The leg, back of the hand, arm and front of the torso are involved; the photo was captured at an angle — 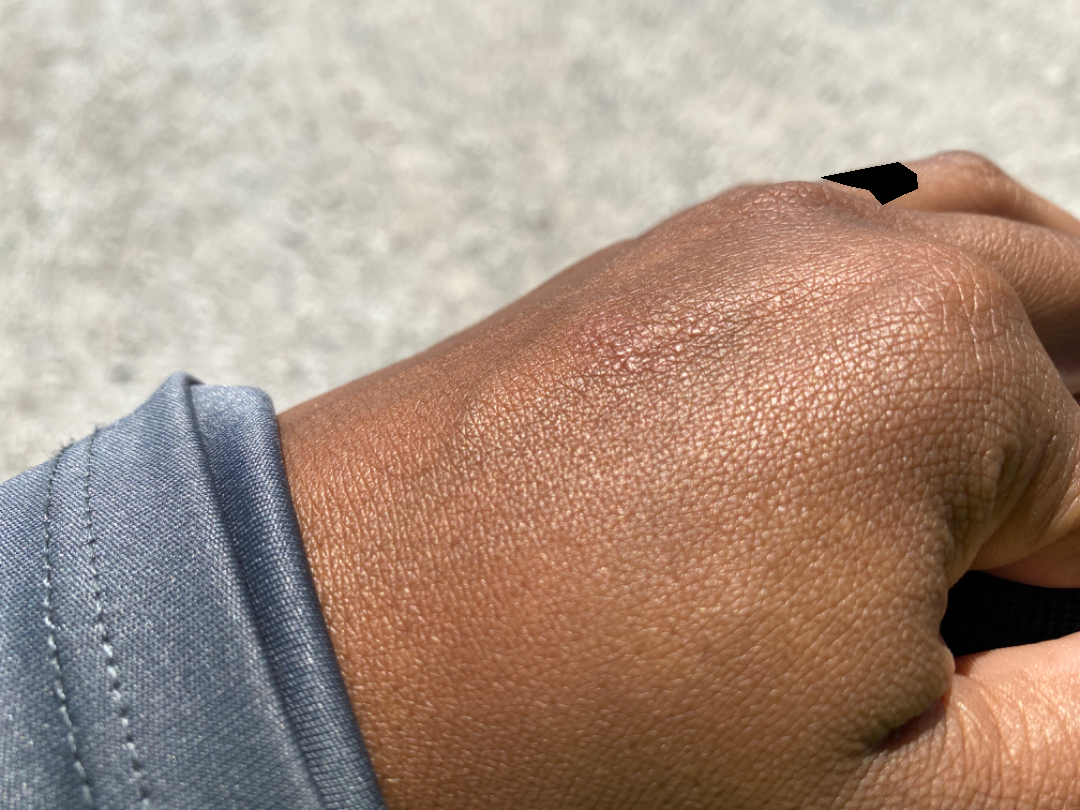assessment=indeterminate from the photograph.